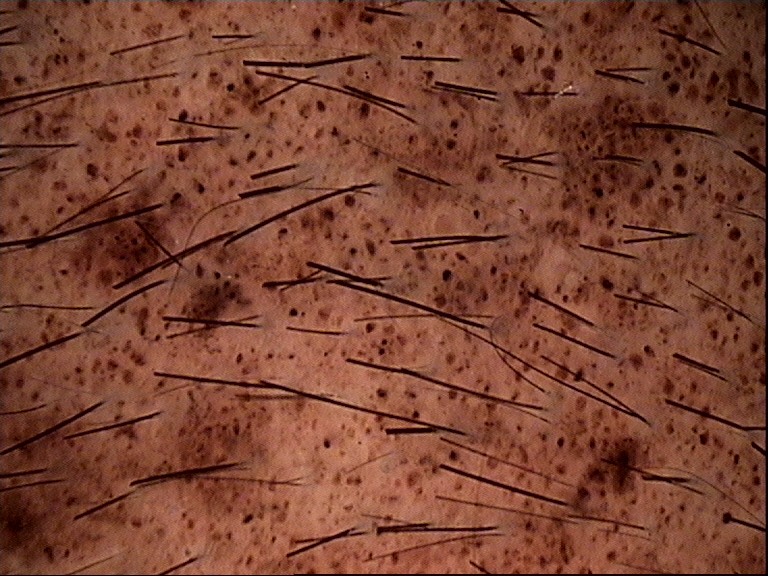Case: Dermoscopy of a skin lesion. Impression: The diagnosis was a banal lesion — a congenital junctional nevus.